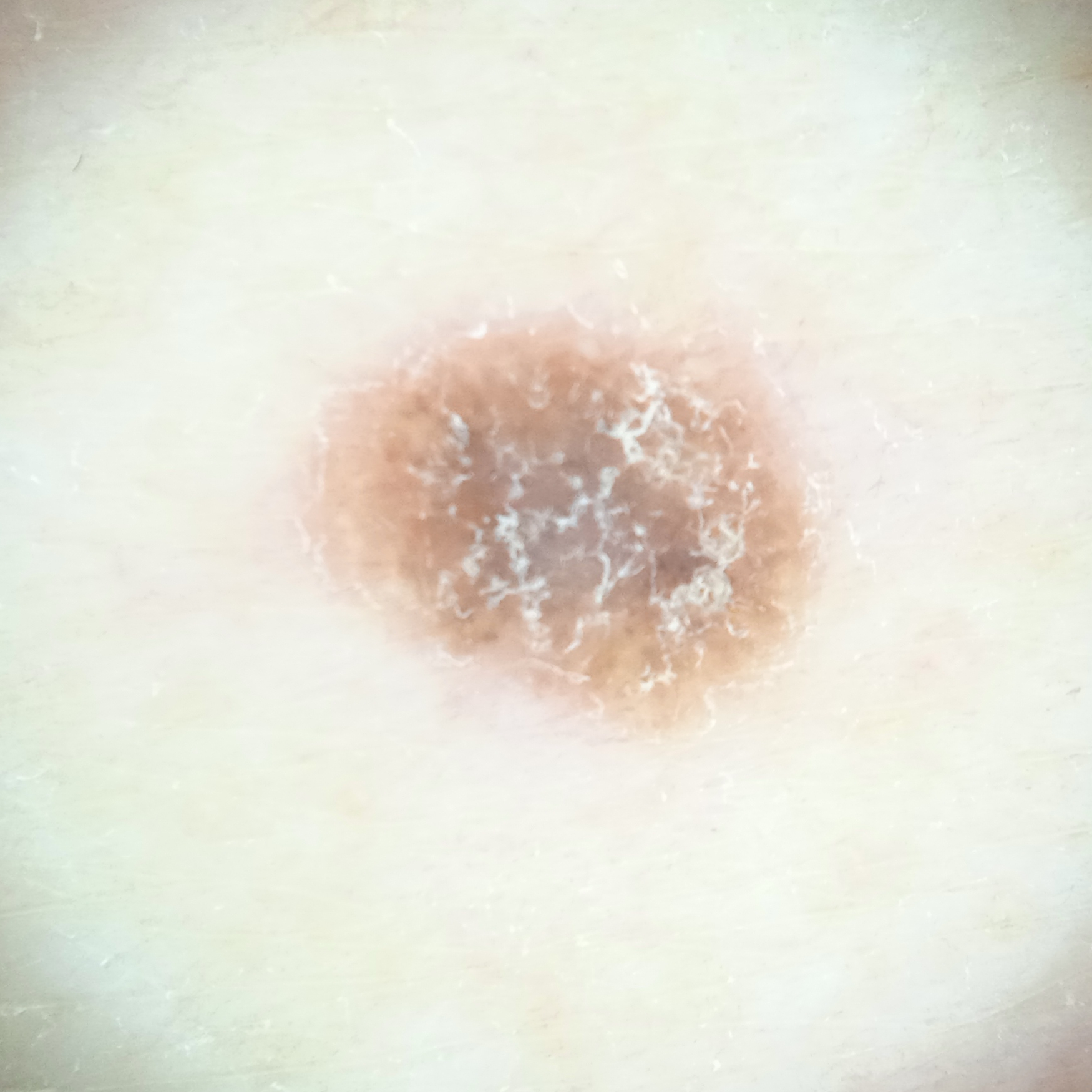By self-report, no personal history of skin cancer.
Few moles overall by the patient's own estimate.
Collected as part of a research study, without a referral diagnosis.
The patient says their skin tans without first burning.
The consensus diagnosis for this lesion was a seborrheic keratosis.